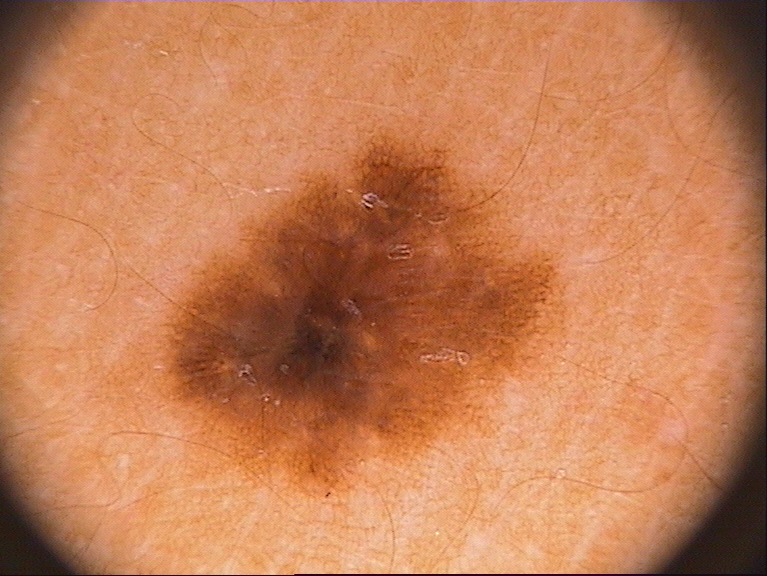<record>
  <patient>
    <sex>female</sex>
  </patient>
  <image>
    <modality>dermoscopy</modality>
  </image>
  <dermoscopic_features>
    <present>pigment network</present>
    <absent>milia-like cysts, streaks, globules, negative network</absent>
  </dermoscopic_features>
  <lesion_extent>moderate</lesion_extent>
  <lesion_location>
    <bbox_xyxy>156, 129, 566, 495</bbox_xyxy>
  </lesion_location>
  <diagnosis>
    <name>melanocytic nevus</name>
    <malignancy>benign</malignancy>
    <lineage>melanocytic</lineage>
    <provenance>clinical</provenance>
  </diagnosis>
</record>